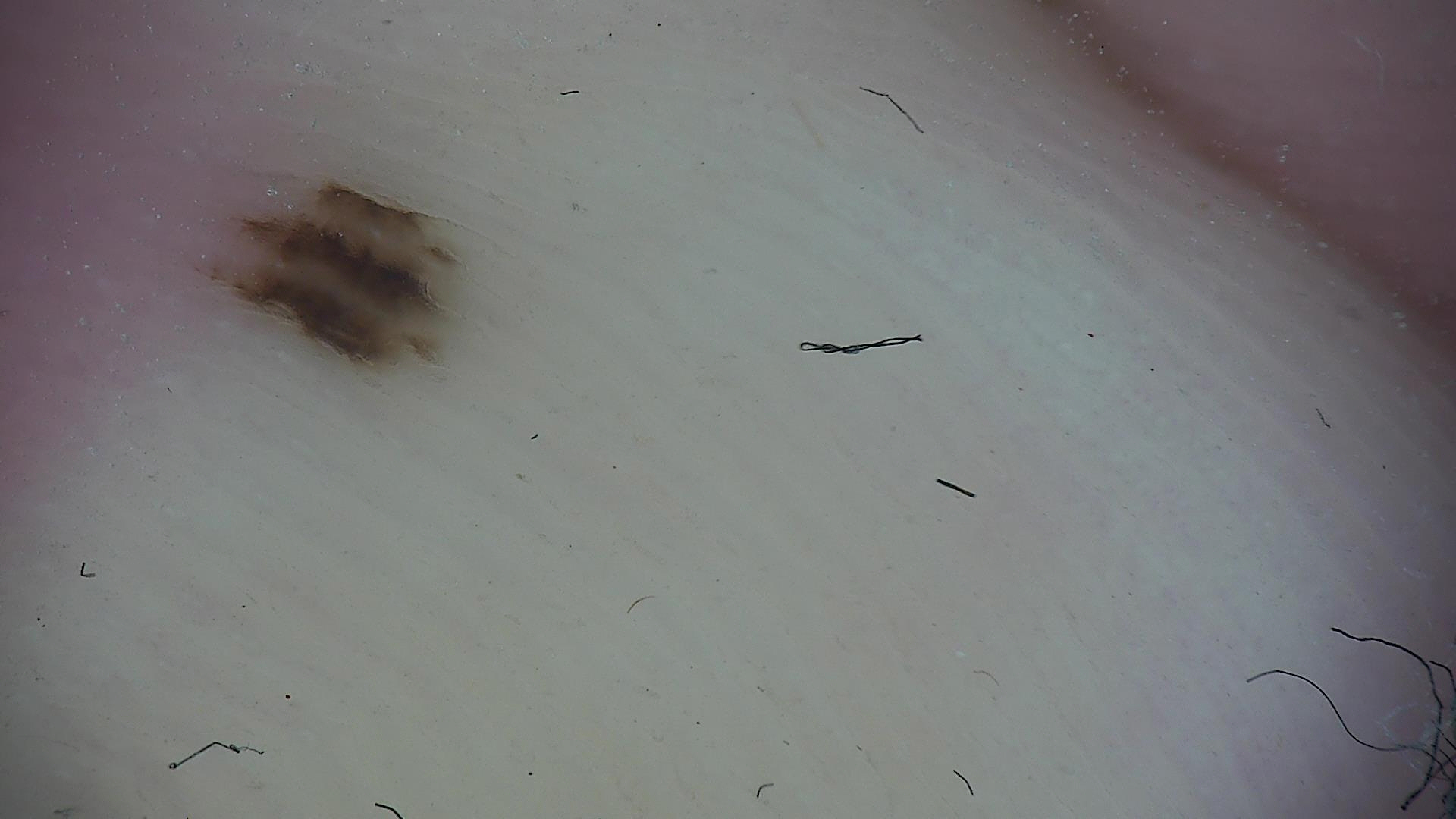Case: A dermoscopic image of a skin lesion. Impression: Classified as a benign lesion — an acral dysplastic junctional nevus.